Dermoscopy of a skin lesion:
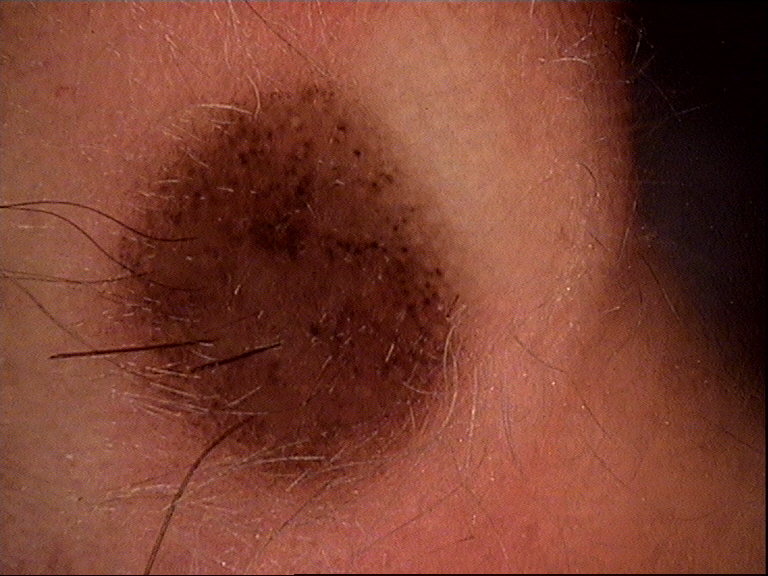{"diagnosis": {"name": "compound nevus", "code": "cb", "malignancy": "benign", "super_class": "melanocytic", "confirmation": "expert consensus"}}